A close-up photograph: 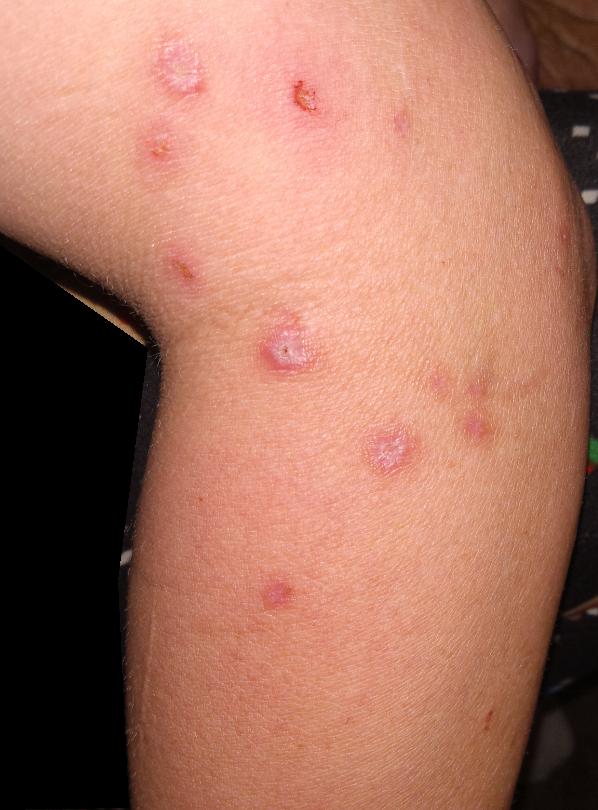{"assessment": "could not be assessed"}